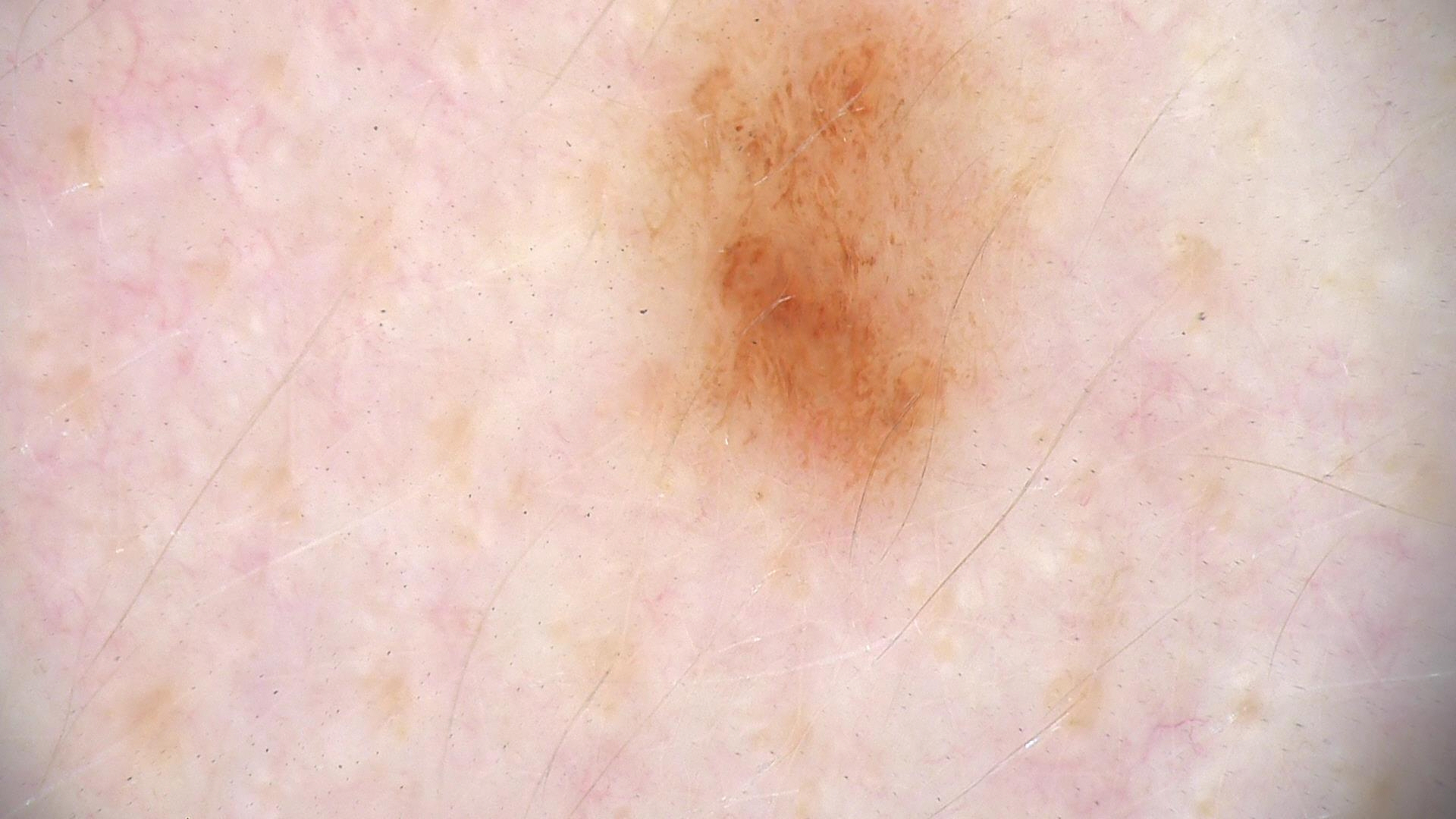diagnosis = dysplastic junctional nevus (expert consensus).